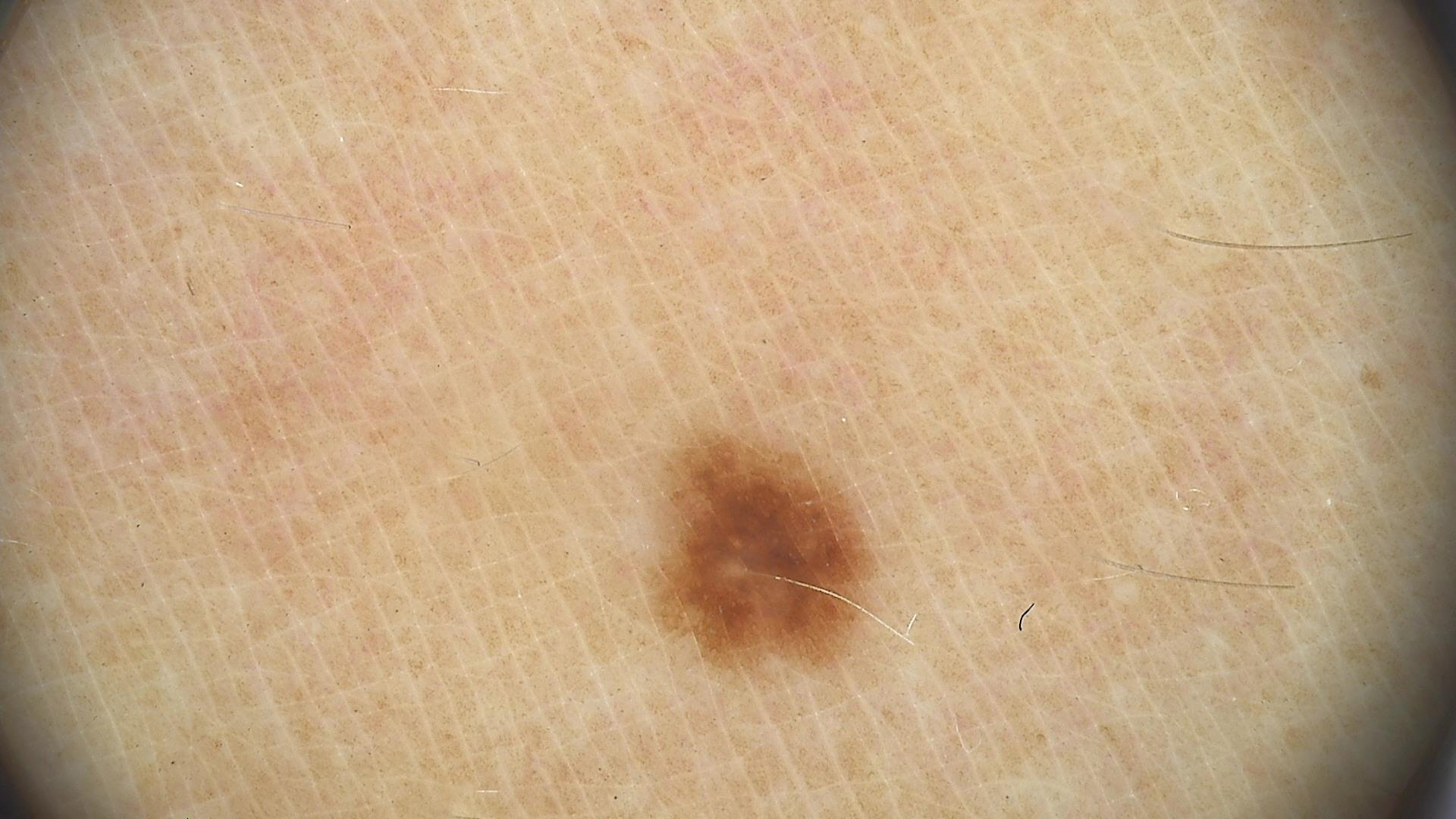class=dysplastic junctional nevus (expert consensus).